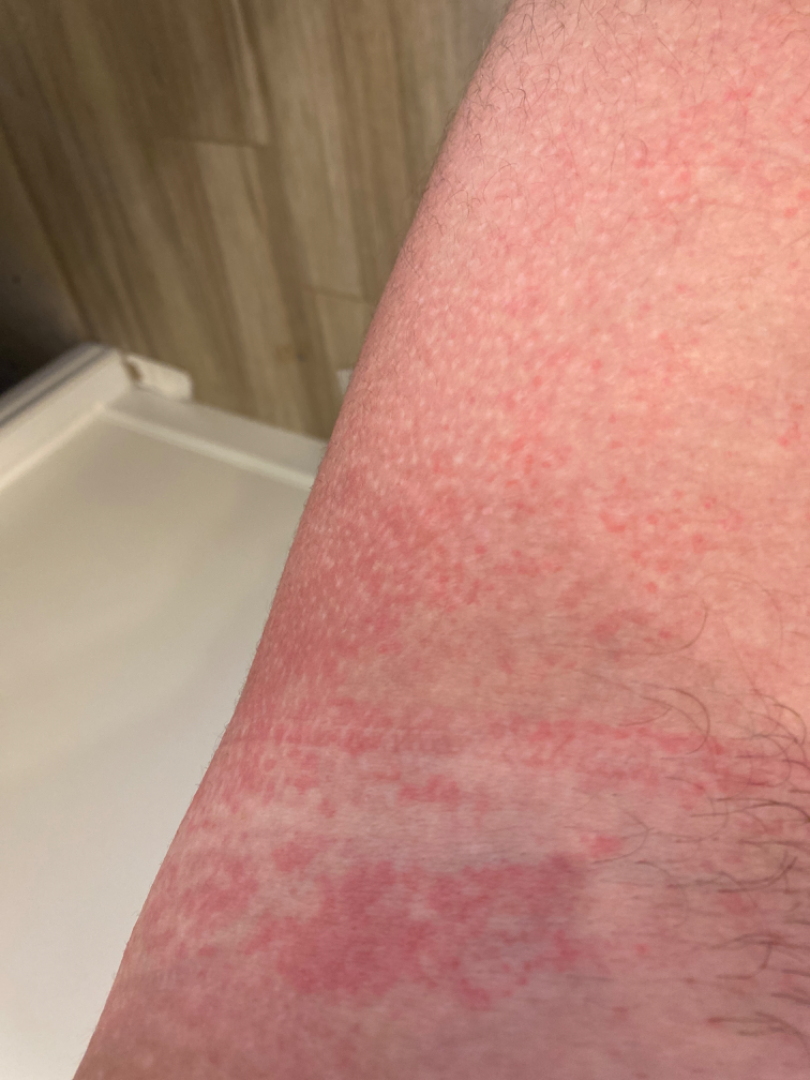  patient_category: a rash
  skin_tone:
    fitzpatrick: III
    monk_skin_tone:
      - 3
      - 4
  shot_type: at an angle
  symptoms: itching
  differential:
    tied_lead:
      - Acute dermatitis, NOS
      - Allergic Contact Dermatitis
      - Irritant Contact Dermatitis